A dermoscopic view of a skin lesion; the subject is a male roughly 55 years of age.
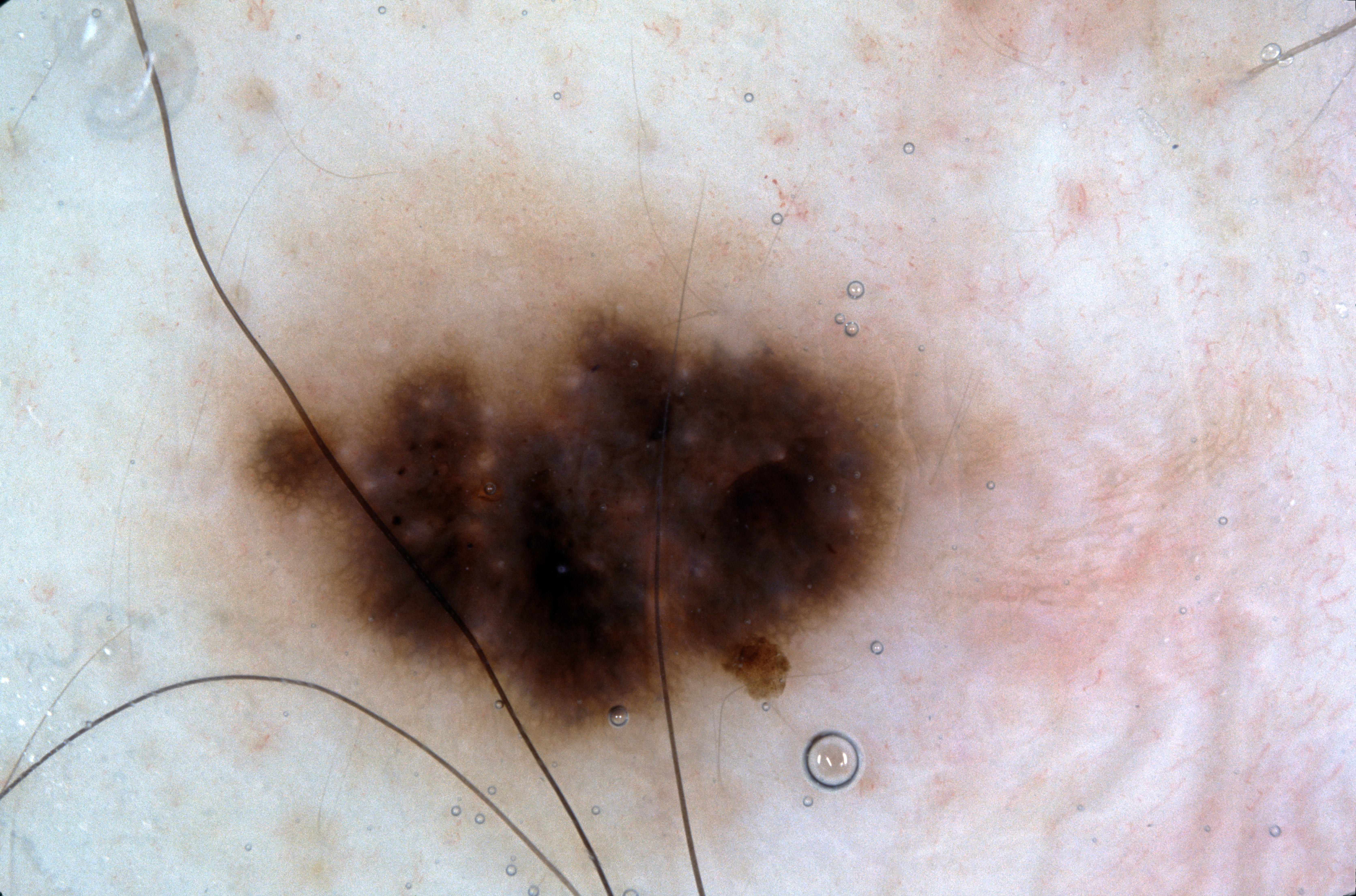Q: Which dermoscopic features were noted?
A: pigment network; absent: milia-like cysts, streaks, and negative network
Q: Where is the lesion located?
A: left=198, top=119, right=1030, bottom=790
Q: Lesion extent?
A: large
Q: What did the assessment conclude?
A: a melanocytic nevus